FST II; the leg is involved; the contributor reports the condition has been present for about one day; no relevant lesion symptoms reported; the lesion is described as raised or bumpy; the photograph is a close-up of the affected area; the subject is male.
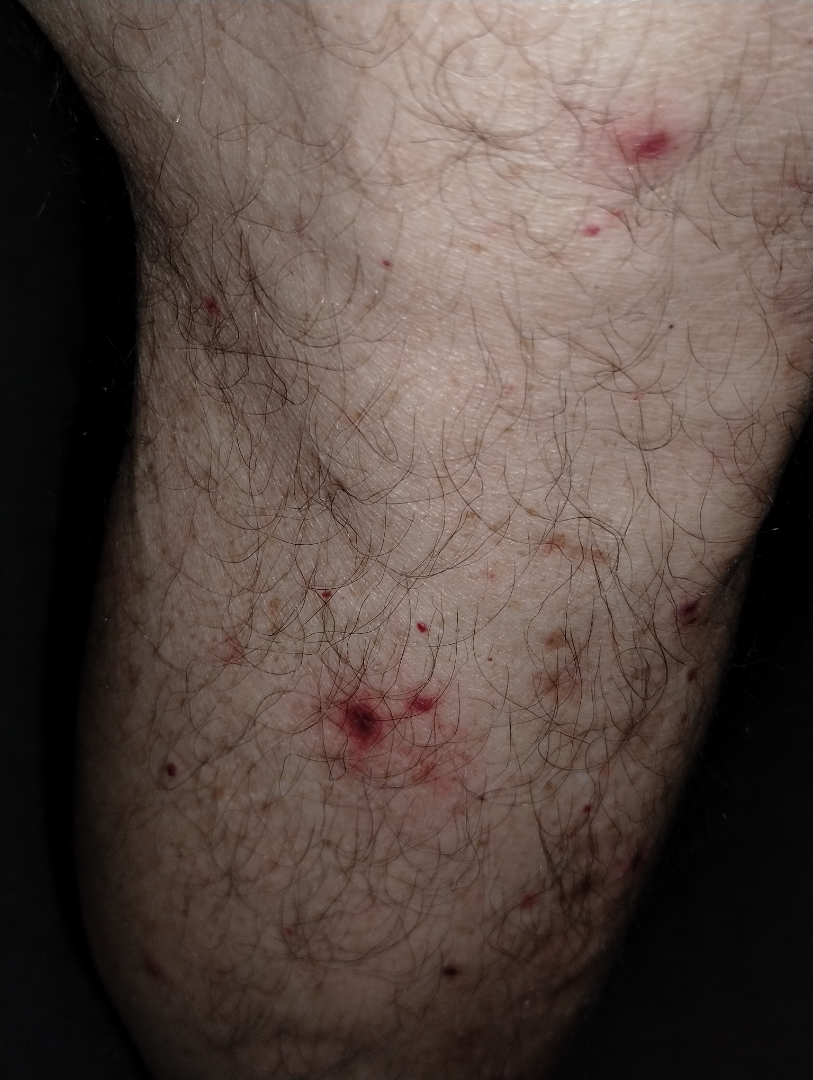<summary>
  <differential>
    <tied_lead>Purpura, Folliculitis</tied_lead>
    <unlikely>Pseudolymphoma, Insect Bite</unlikely>
  </differential>
</summary>